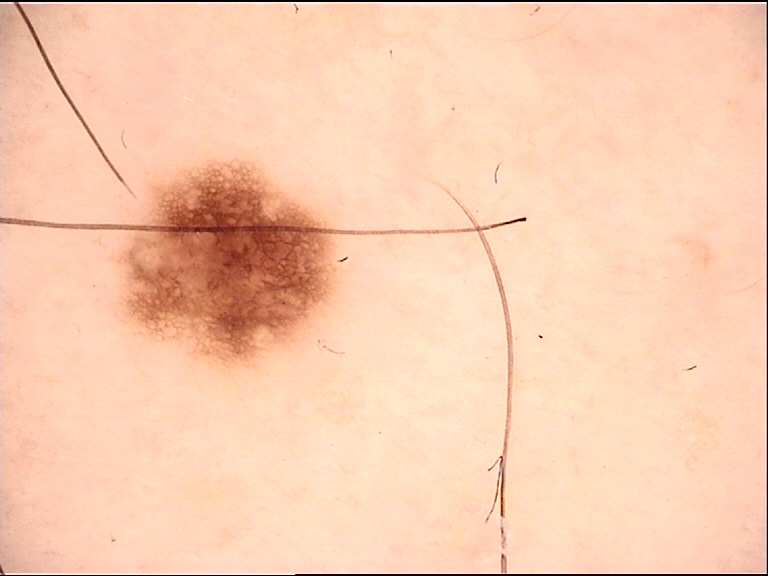Impression: The diagnosis was a dysplastic junctional nevus.